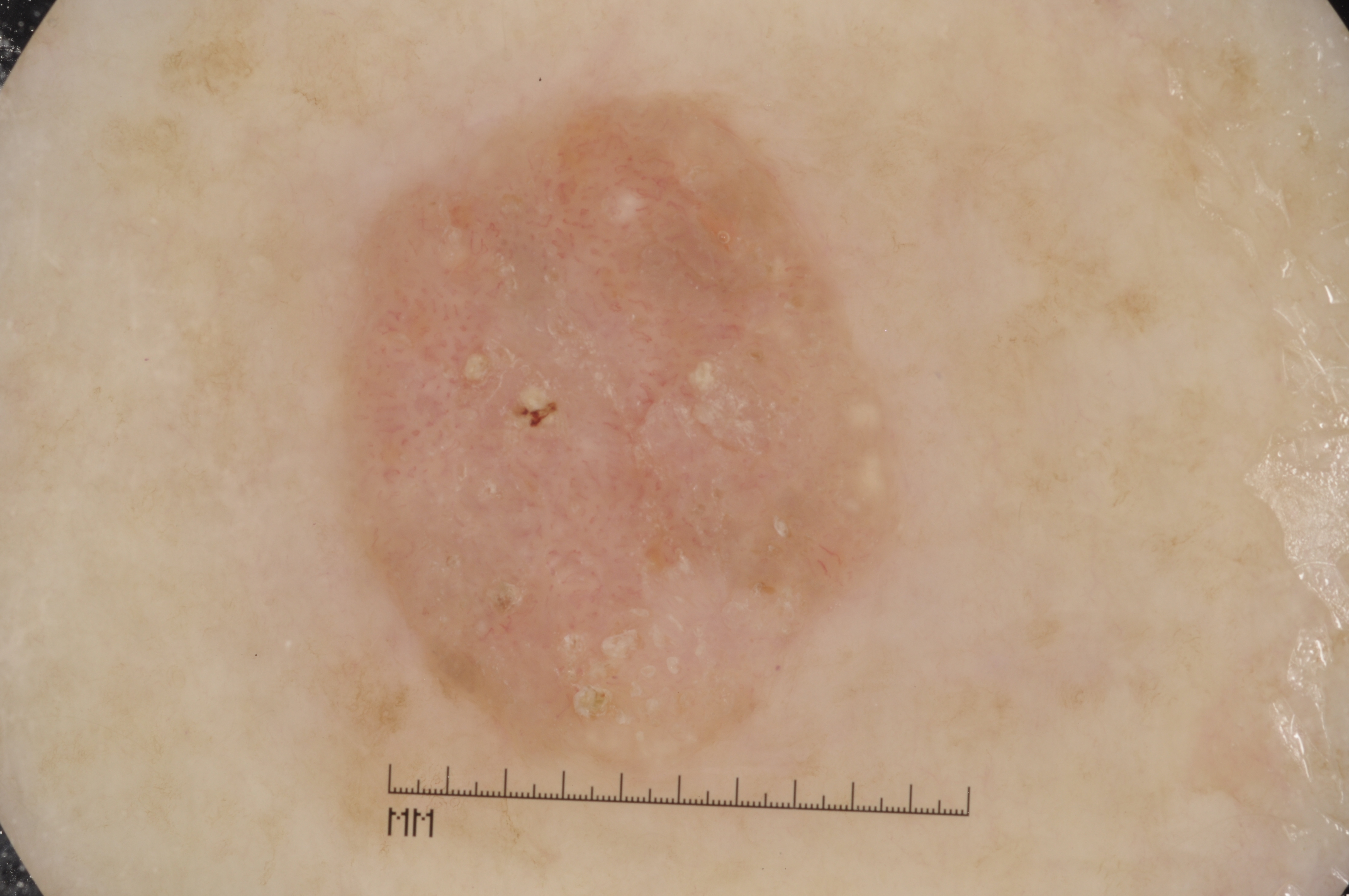Q: Who is the patient?
A: female, aged around 70
Q: What is the imaging modality?
A: dermoscopy
Q: What is the lesion's bounding box?
A: [319,74,931,794]
Q: What dermoscopic features are present?
A: milia-like cysts; absent: streaks, negative network, and pigment network
Q: What is the diagnosis?
A: a seborrheic keratosis